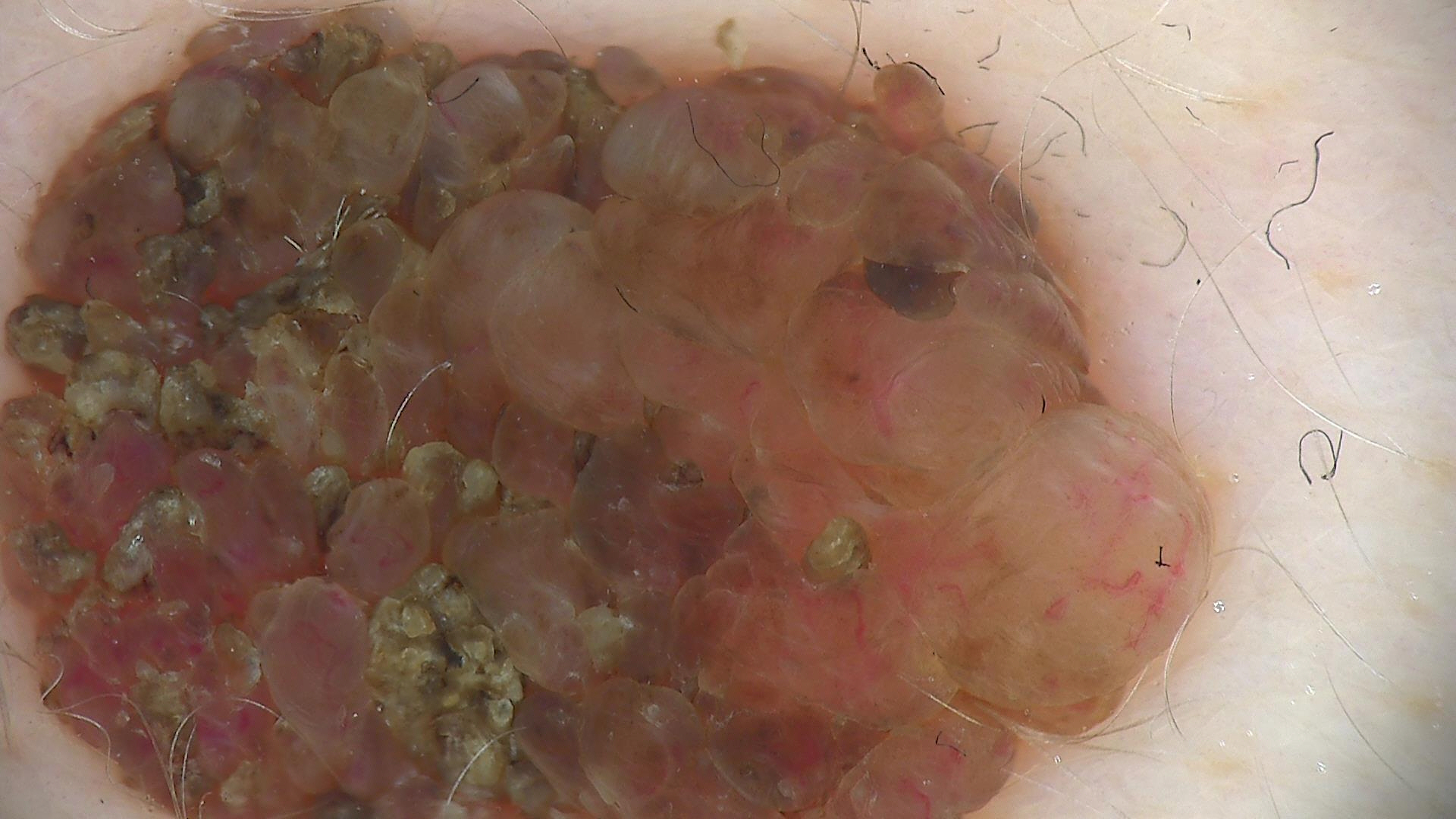Conclusion: Diagnosed as a dermal nevus.